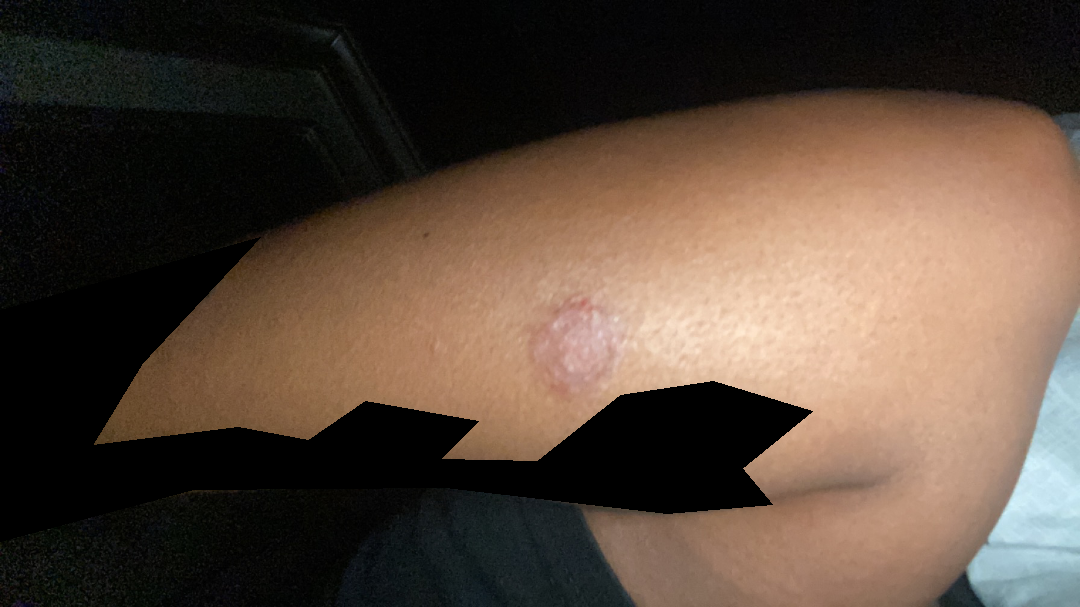No differential diagnosis could be assigned on photographic review.